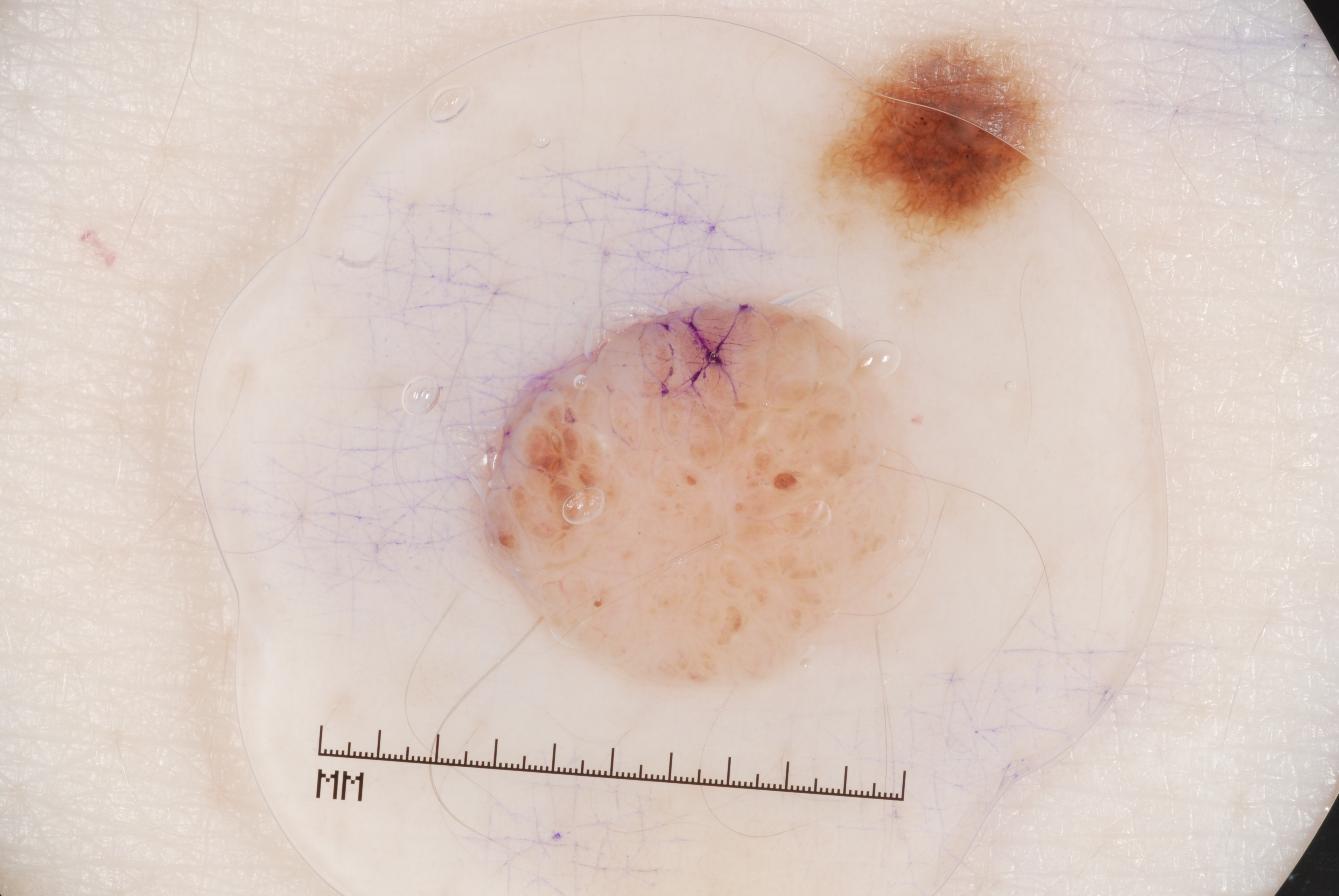image type = dermoscopy
patient = female, in their 60s
extent = ~11% of the field
dermoscopic pattern = milia-like cysts; absent: negative network, streaks, and pigment network
lesion bbox = bbox(469, 292, 938, 688)
diagnosis = a melanocytic nevus